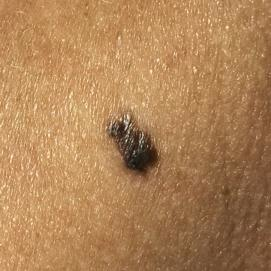A smartphone photograph of a skin lesion. The chart notes prior malignancy (patient or family), no tobacco use, and no pesticide exposure. The lesion is on the neck. Confirmed on histopathology as a seborrheic keratosis.